The leg is involved; a close-up photograph.
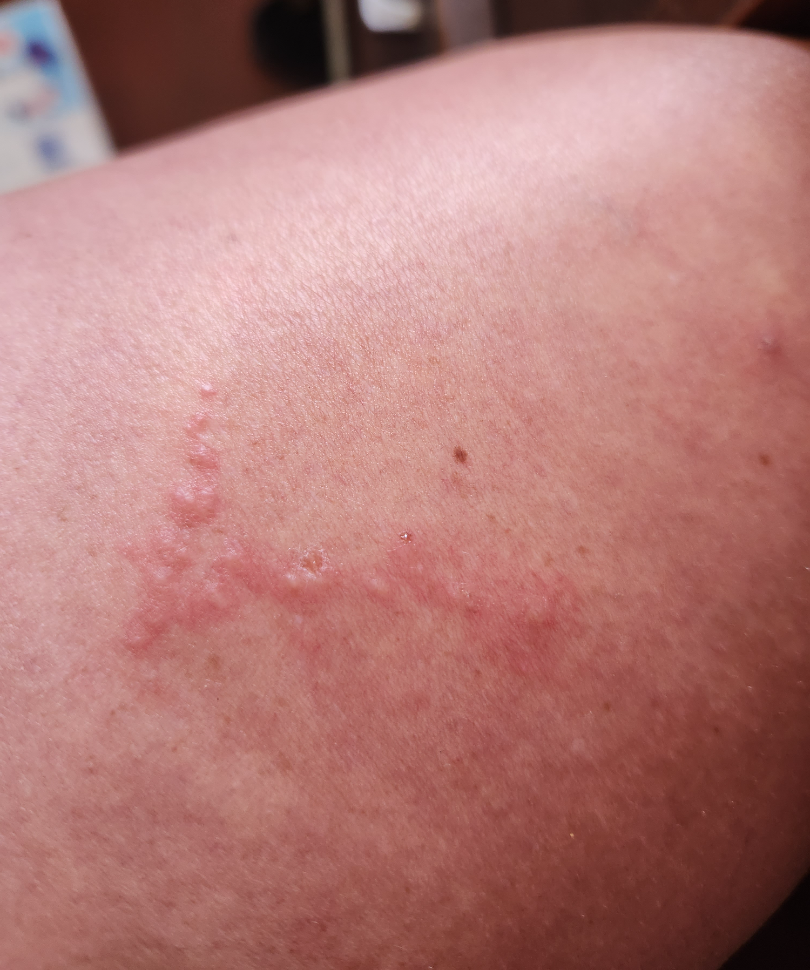Cutaneous larva migrans (33%); Herpes Simplex (33%); Allergic Contact Dermatitis (33%).